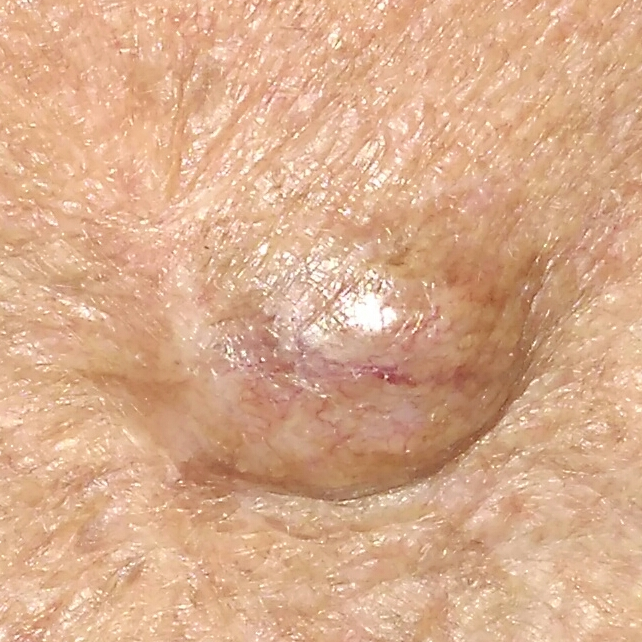pathology: basal cell carcinoma (biopsy-proven).